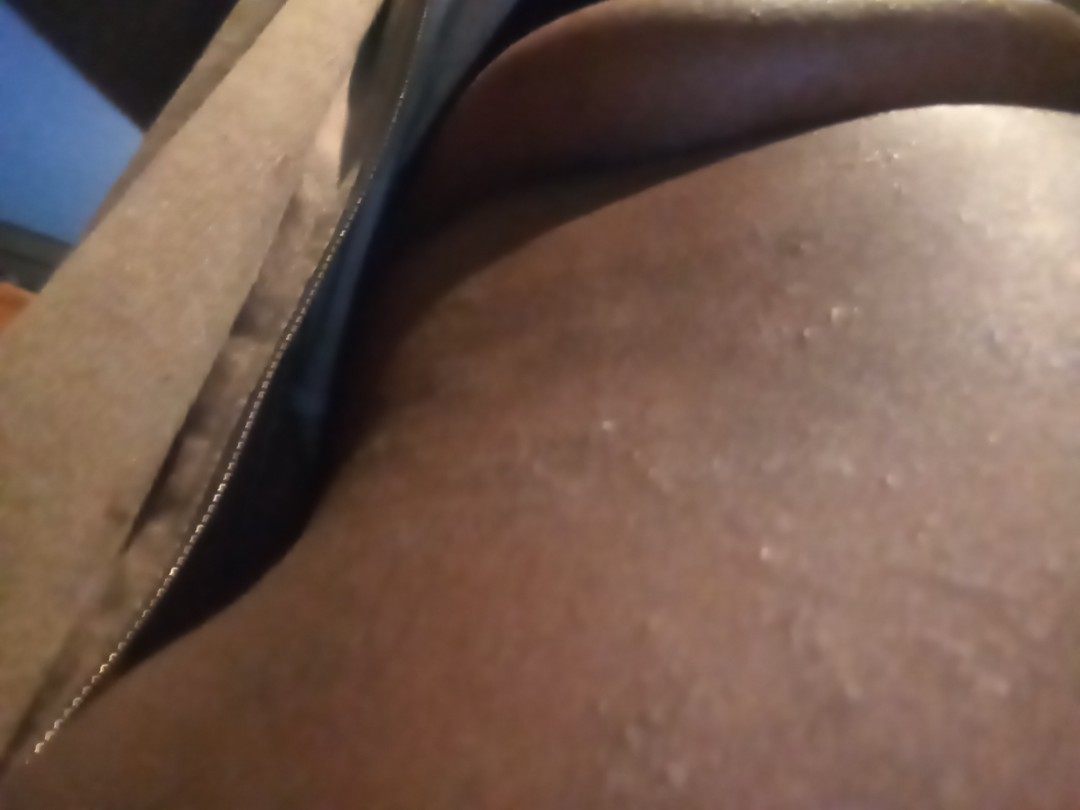Assessment: The case was difficult to assess from the available photograph. Clinical context: The patient reports itching, enlargement, darkening and bothersome appearance. The patient reports the lesion is rough or flaky and raised or bumpy. The subject is 30–39, female. Located on the front of the torso and arm. This is a close-up image. Self-categorized by the patient as a rash. Present for one to four weeks.